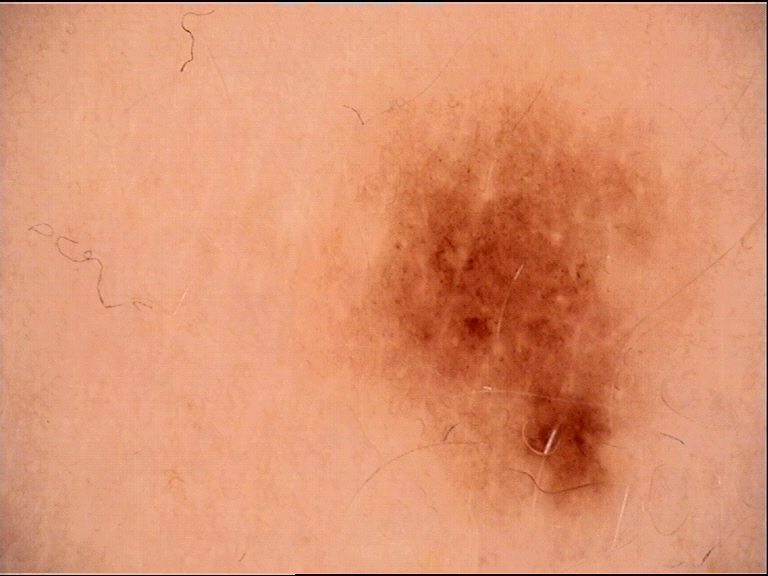imaging: dermatoscopy; label: dysplastic junctional nevus (expert consensus).